The photograph is a close-up of the affected area: 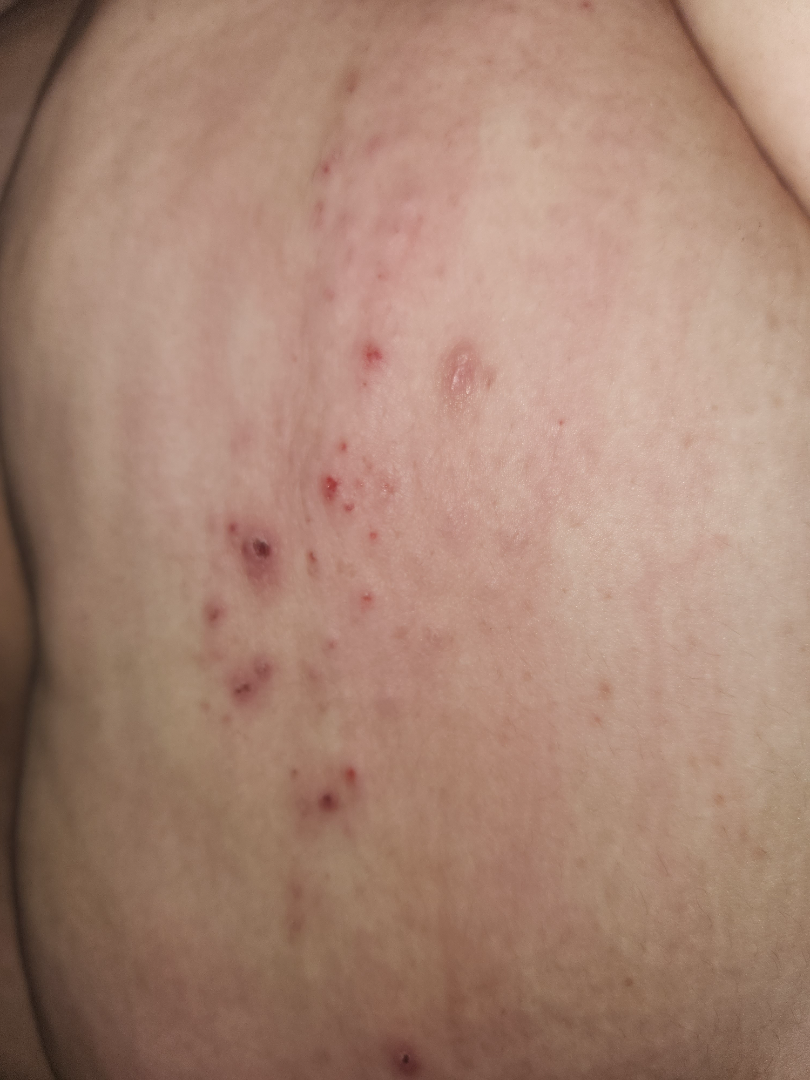The reviewing clinician's impression was: the leading consideration is Allergic Contact Dermatitis; an alternative is Bullous Pemphigoid; the differential also includes Insect Bite.